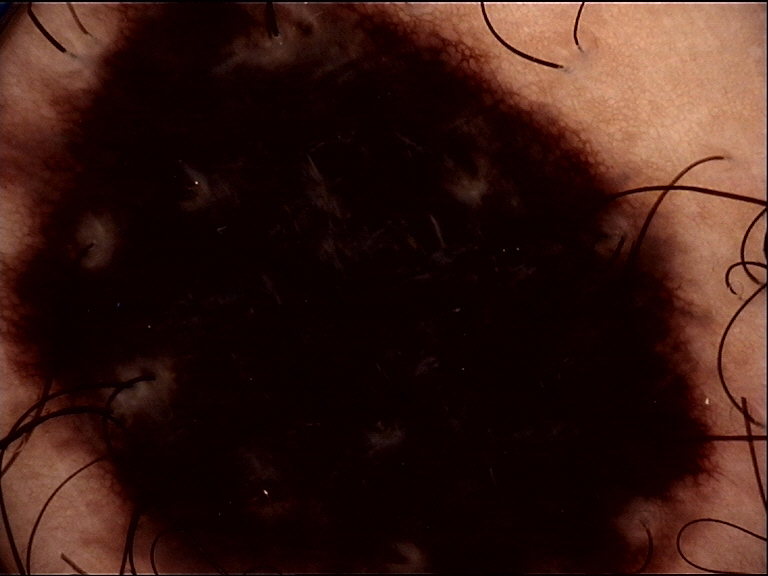  diagnosis:
    name: dysplastic compound nevus
    code: cd
    malignancy: benign
    super_class: melanocytic
    confirmation: expert consensus